Imaged for a research study, with no referral diagnosis recorded; by self-report, immunosuppression, a family history of skin cancer, and a personal history of skin cancer; the patient describes having numerous moles; a male subject age 65.
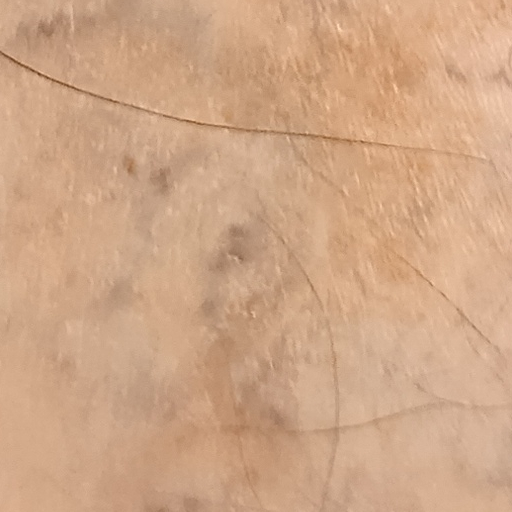Case:
• diameter · 13 mm
• diagnostic label · basal cell carcinoma (dermatologist consensus)